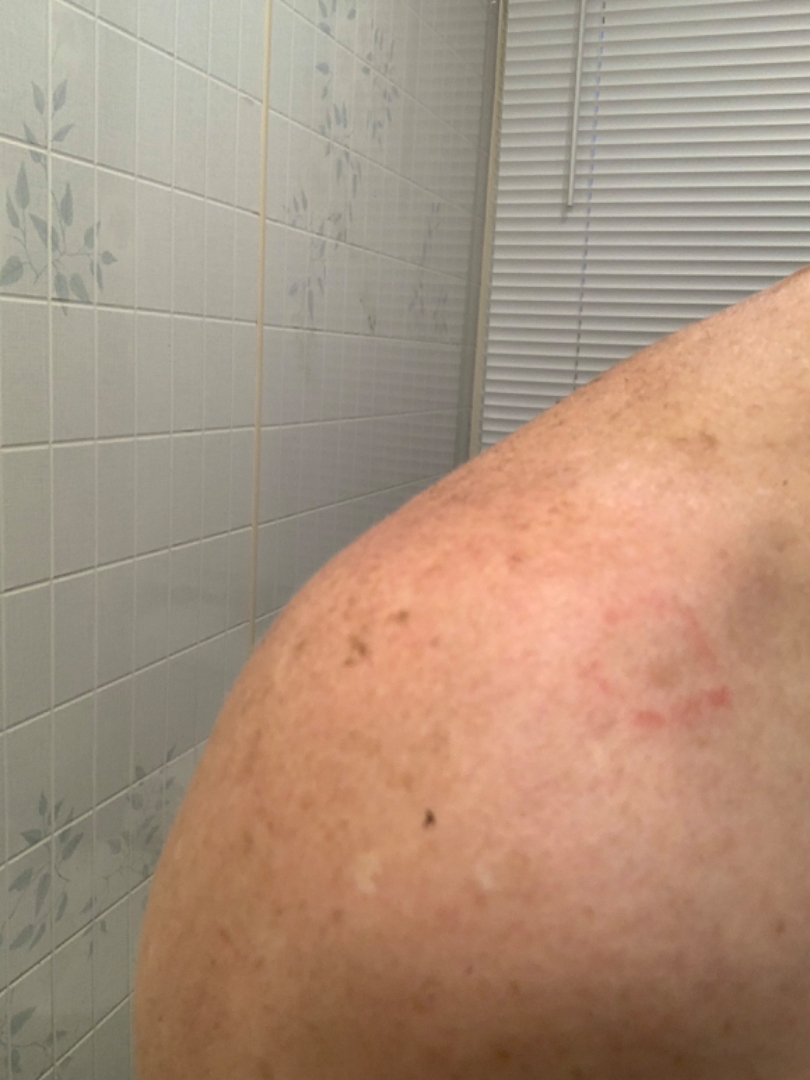contributor: female
skin tone: FST III; non-clinician graders estimated a Monk skin tone scale of 4
lesion texture: flat
body site: arm
duration: one to three months
photo taken: close-up